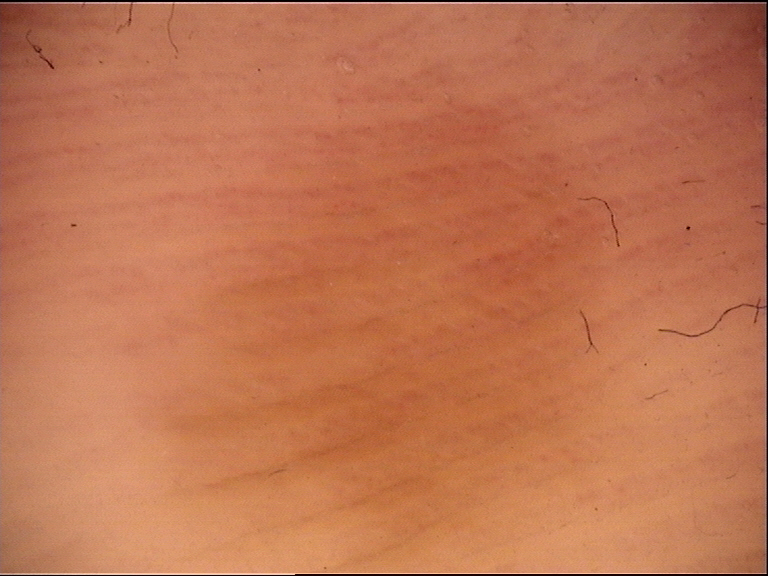A dermoscopic image of a skin lesion.
Diagnosed as a benign lesion — an acral dysplastic junctional nevus.